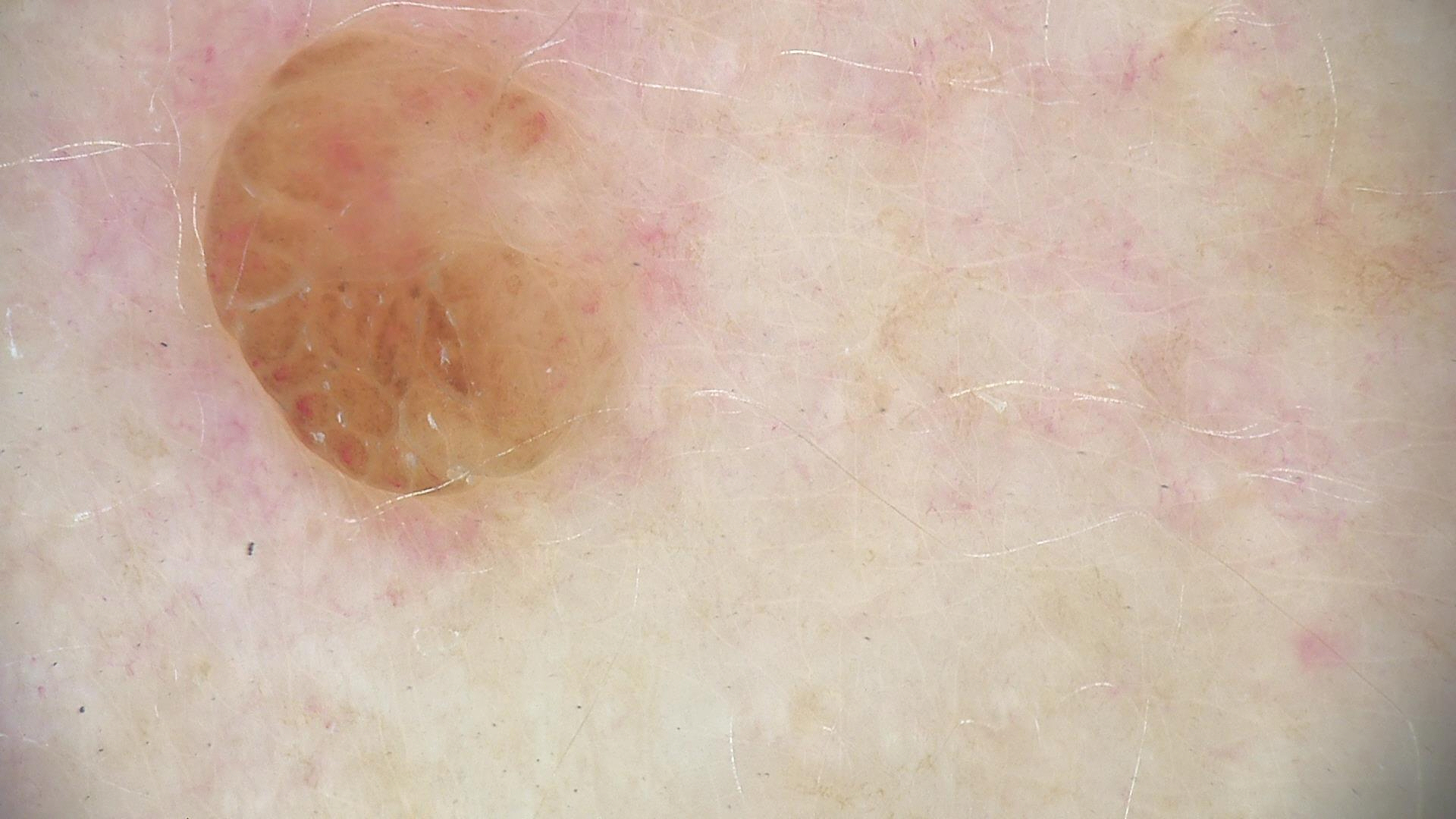label = dermal nevus (expert consensus).